A male subject aged 53; a clinical close-up photograph of a skin lesion — 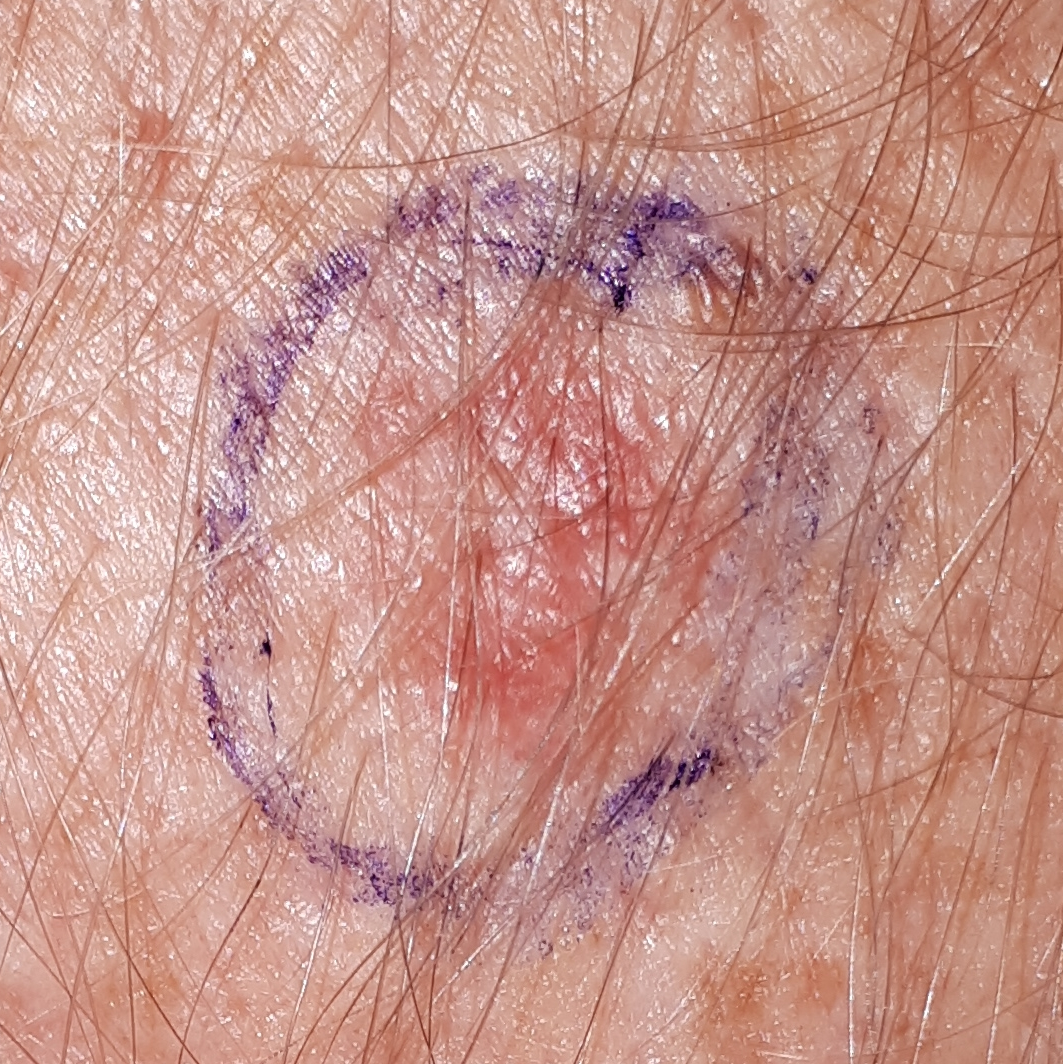The lesion is located on the face.
The patient describes that the lesion itches, is elevated, has grown, hurts, and has bled.
The biopsy diagnosis was a basal cell carcinoma.